A male patient 68 years old. A clinical close-up photograph of a skin lesion:
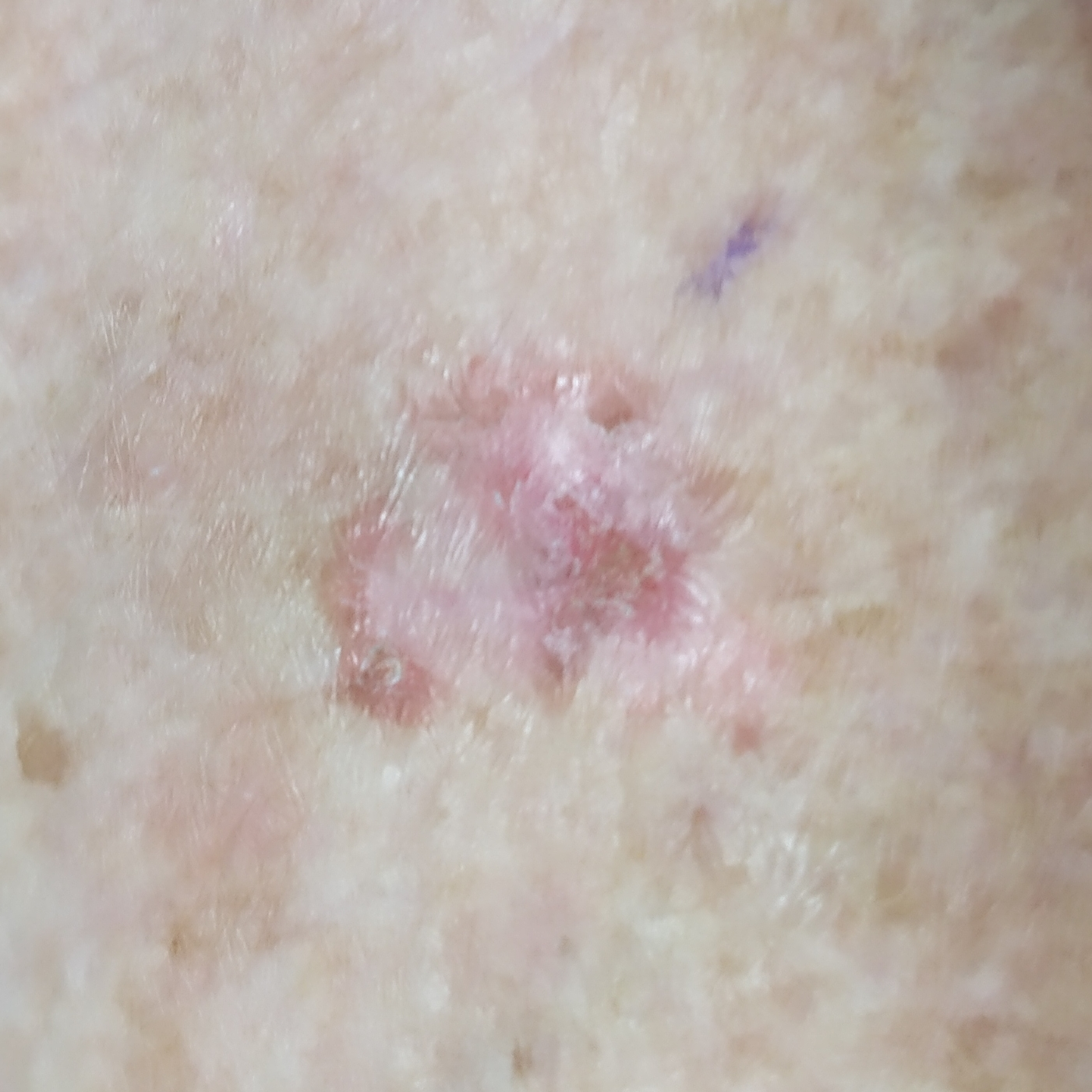Case:
- region: a forearm
- symptoms: no bleeding, no itching
- diagnosis: squamous cell carcinoma (biopsy-proven)